A dermoscopy image of a single skin lesion: 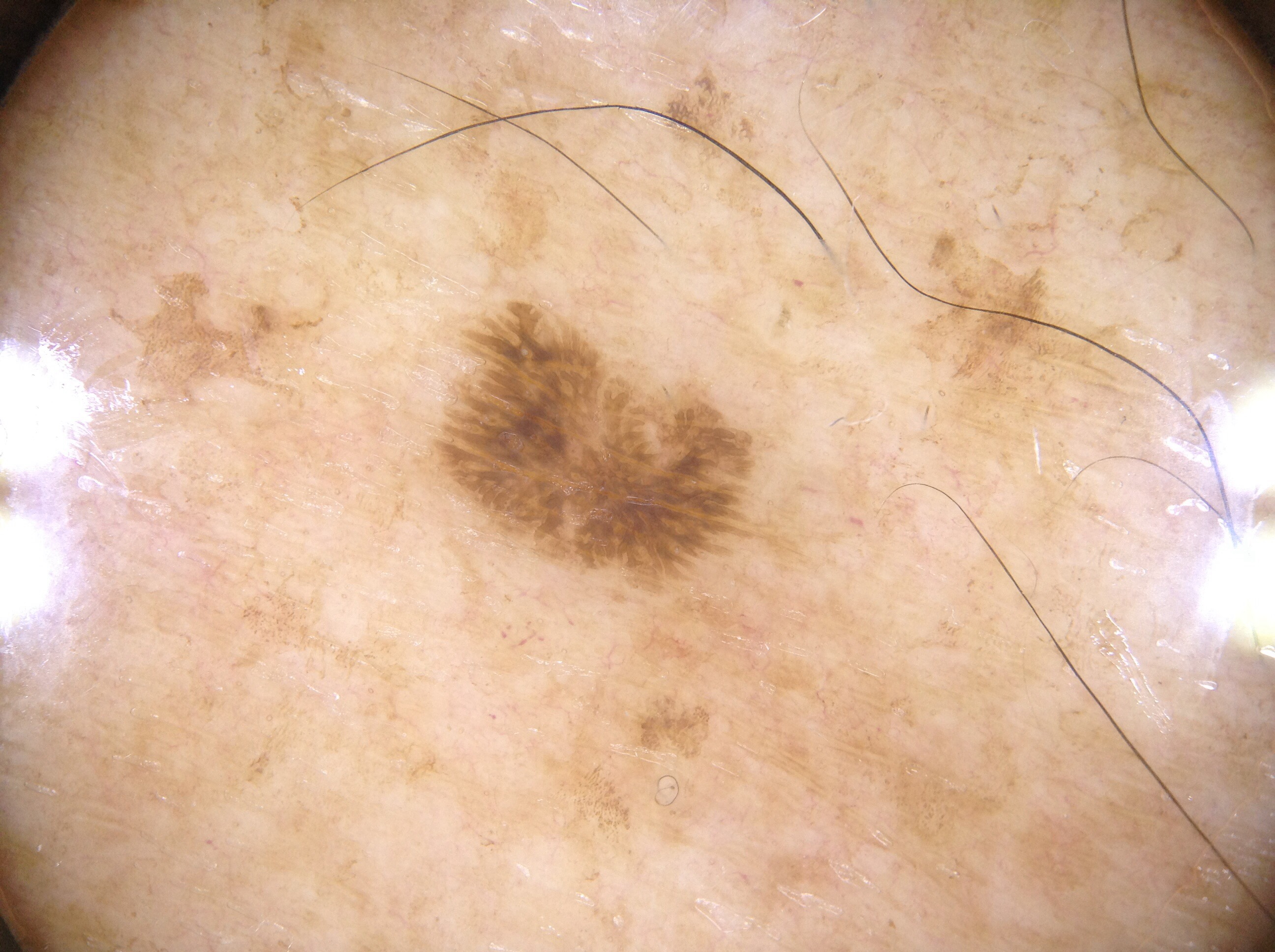  dermoscopic_features:
    present: []
    absent:
      - pigment network
      - negative network
      - milia-like cysts
      - streaks
  lesion_location:
    bbox_xyxy:
      - 435
      - 301
      - 780
      - 595
  diagnosis:
    name: seborrheic keratosis
    malignancy: benign
    lineage: keratinocytic
    provenance: clinical